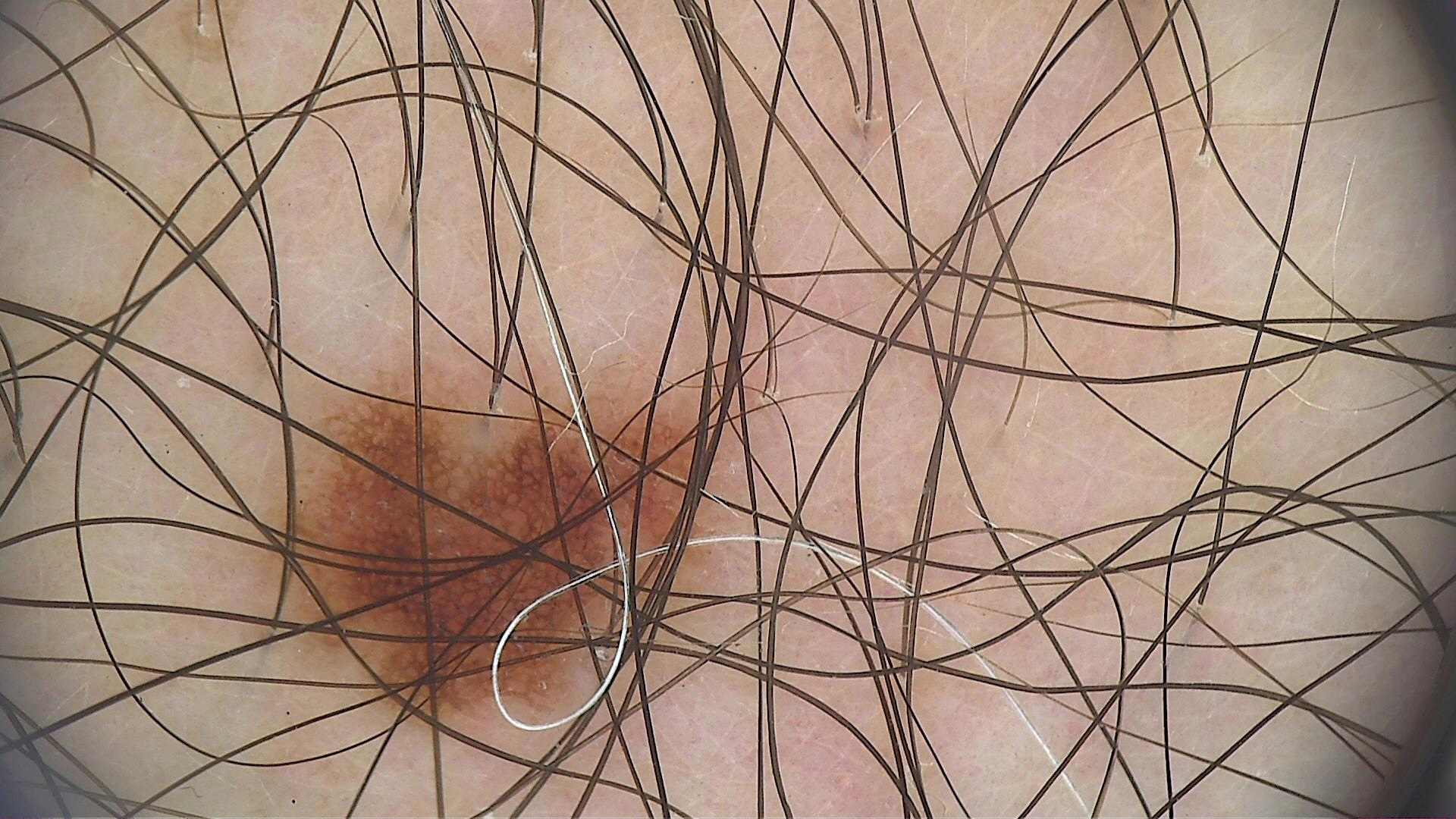Case:
* modality — dermoscopy
* class — dysplastic junctional nevus (expert consensus)